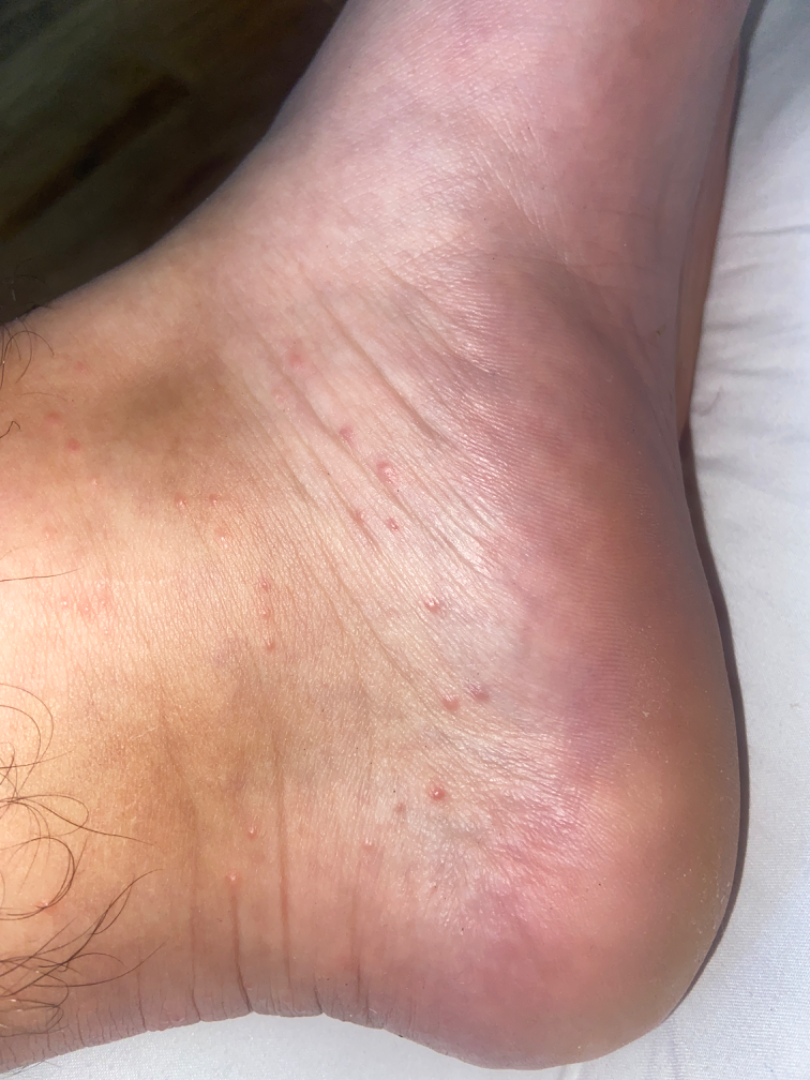Findings:
The skin condition could not be confidently assessed from this image.
Background:
The lesion is associated with itching. A close-up photograph. The patient notes the lesion is raised or bumpy. Located on the top or side of the foot.